This is a dermoscopic photograph of a skin lesion — 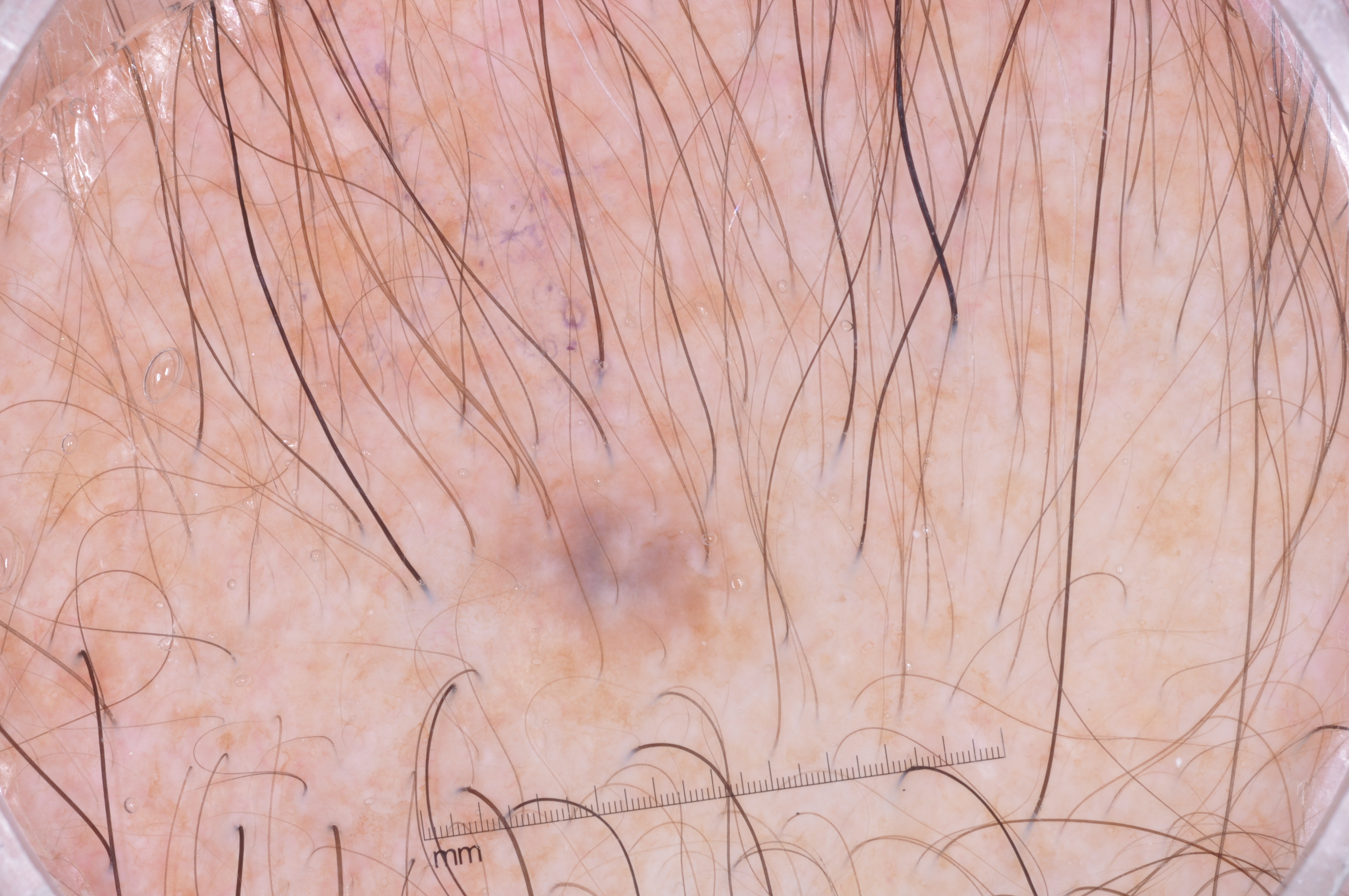Dermoscopic assessment notes milia-like cysts, with no streaks, pigment network, or negative network.
In (x1, y1, x2, y2) order, lesion location: <bbox>464, 413, 790, 686</bbox>.
The lesion takes up about 5% of the image.
The diagnostic assessment was a melanocytic nevus.